The photo was captured at a distance · the lesion involves the arm.
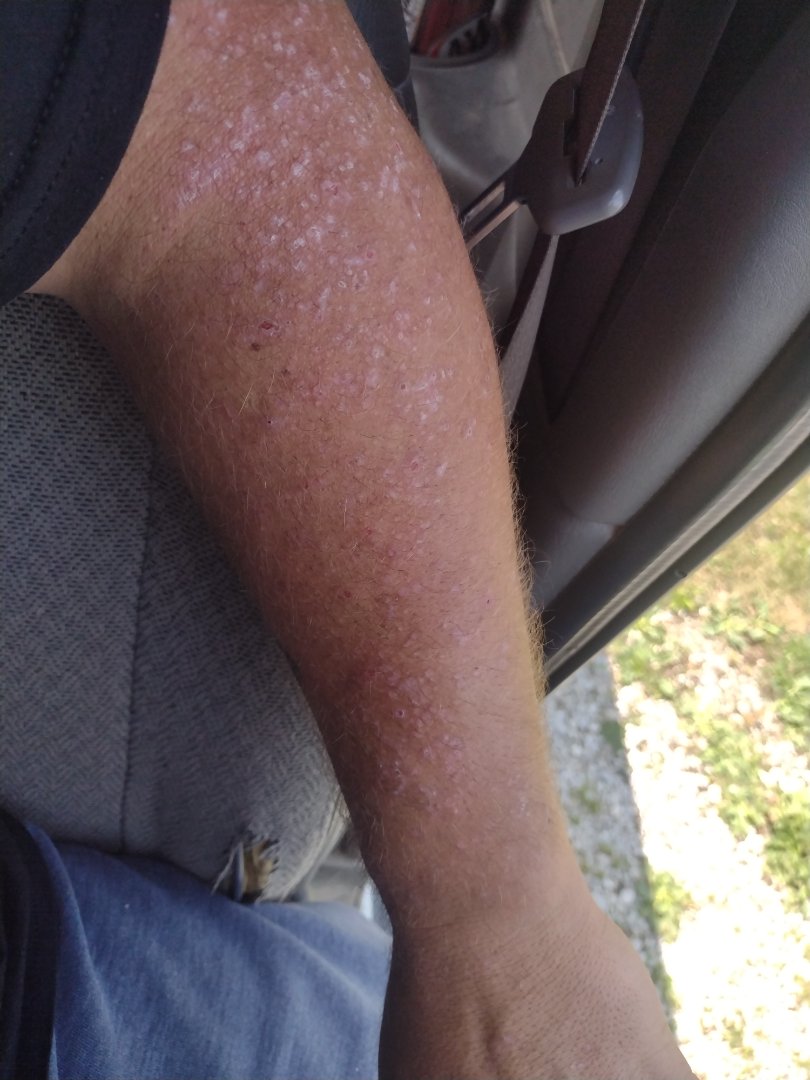Q: How does the lesion feel?
A: raised or bumpy and rough or flaky
Q: What conditions are considered?
A: most likely Psoriasis; also raised was Drug Rash